A dermoscopy image of a single skin lesion.
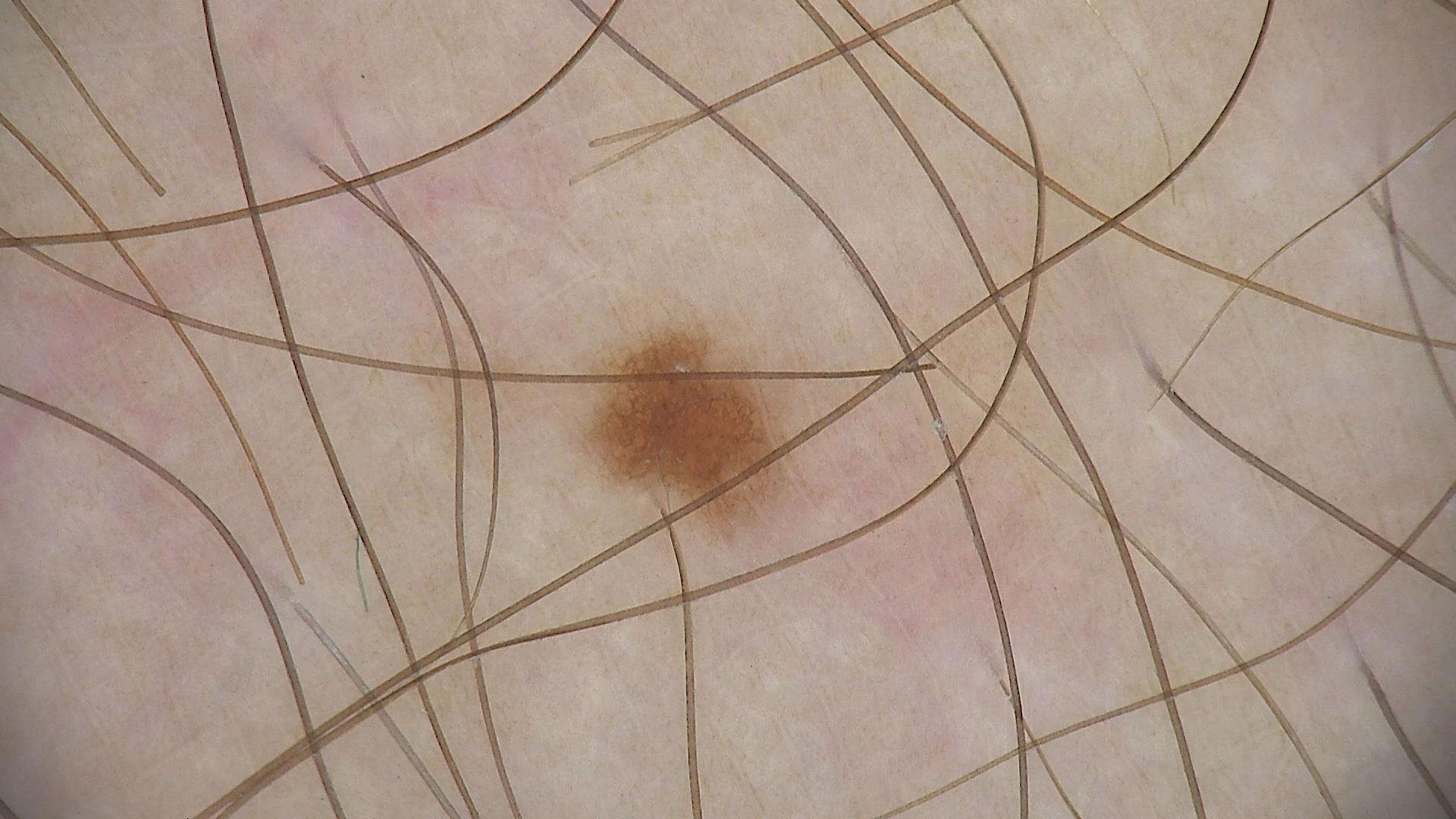Q: What kind of lesion is this?
A: banal
Q: What was the diagnostic impression?
A: junctional nevus (expert consensus)